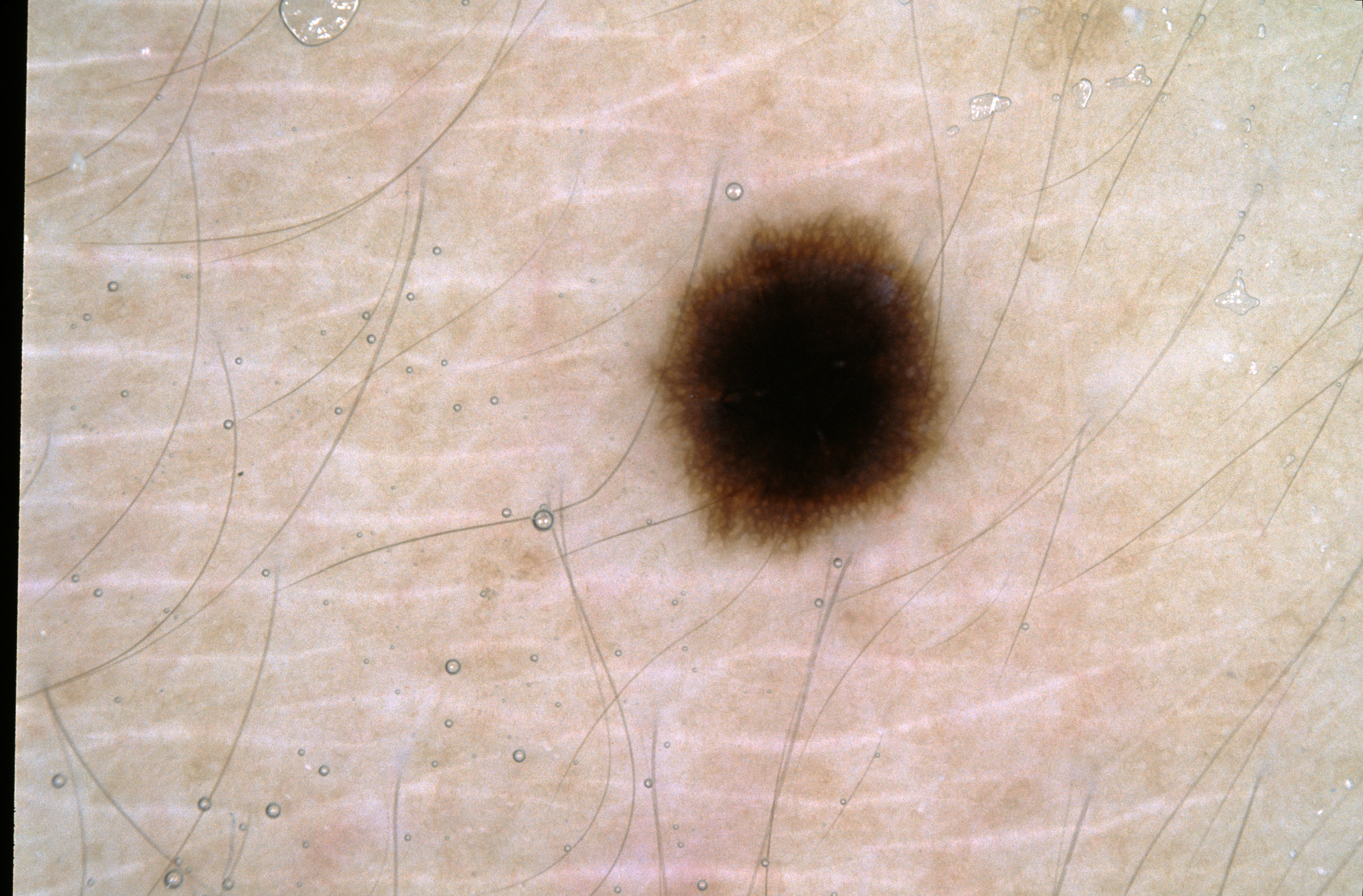{
  "image": {
    "modality": "dermoscopy"
  },
  "patient": {
    "sex": "female",
    "age_approx": 30
  },
  "dermoscopic_features": {
    "present": [
      "pigment network"
    ],
    "absent": [
      "streaks",
      "negative network",
      "milia-like cysts"
    ]
  },
  "lesion_location": {
    "bbox_xyxy": [
      649,
      210,
      948,
      553
    ]
  },
  "diagnosis": {
    "name": "melanocytic nevus",
    "malignancy": "benign",
    "lineage": "melanocytic",
    "provenance": "clinical"
  }
}